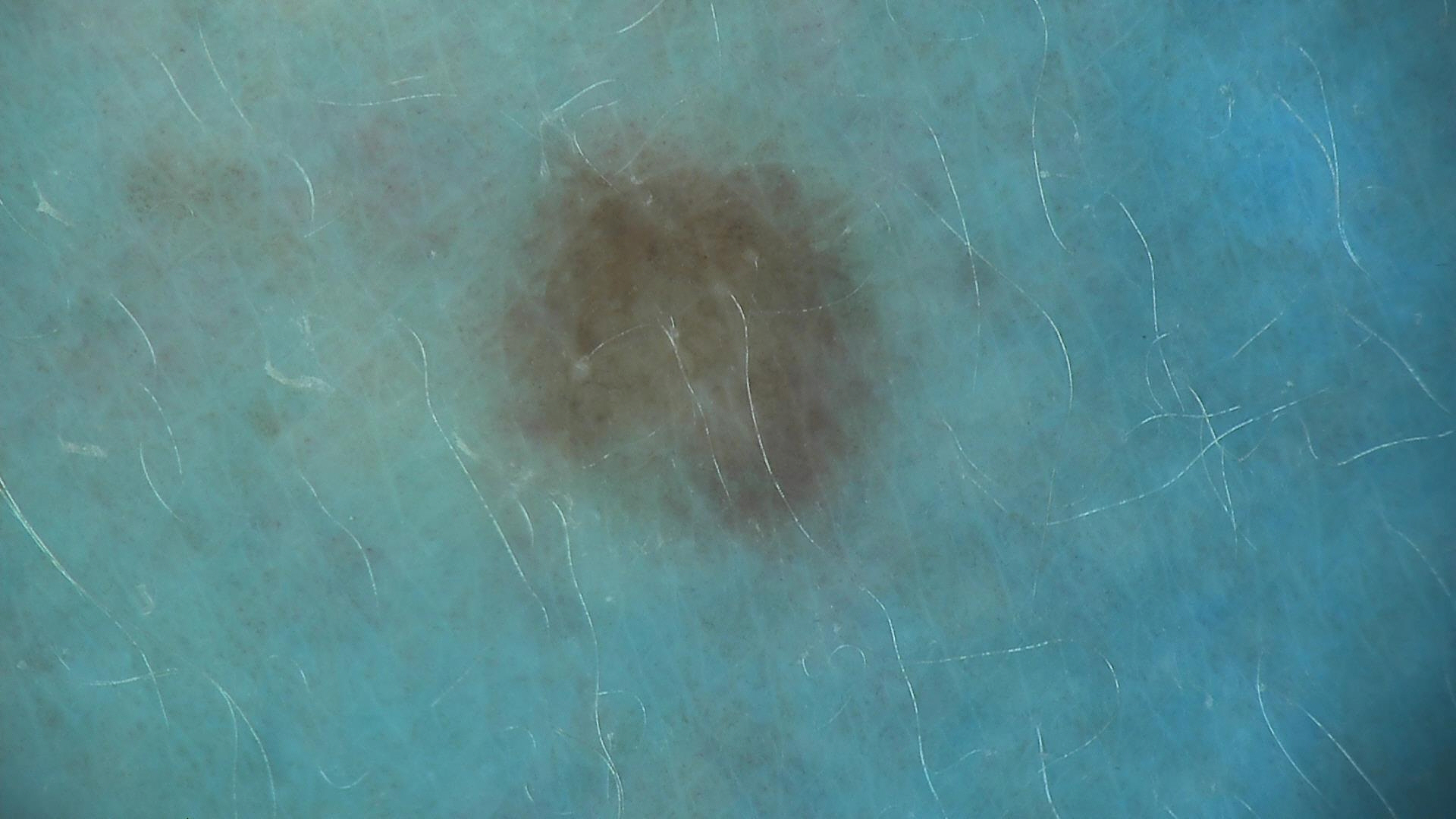Case: A skin lesion imaged with a dermatoscope. Conclusion: Labeled as a dysplastic junctional nevus.